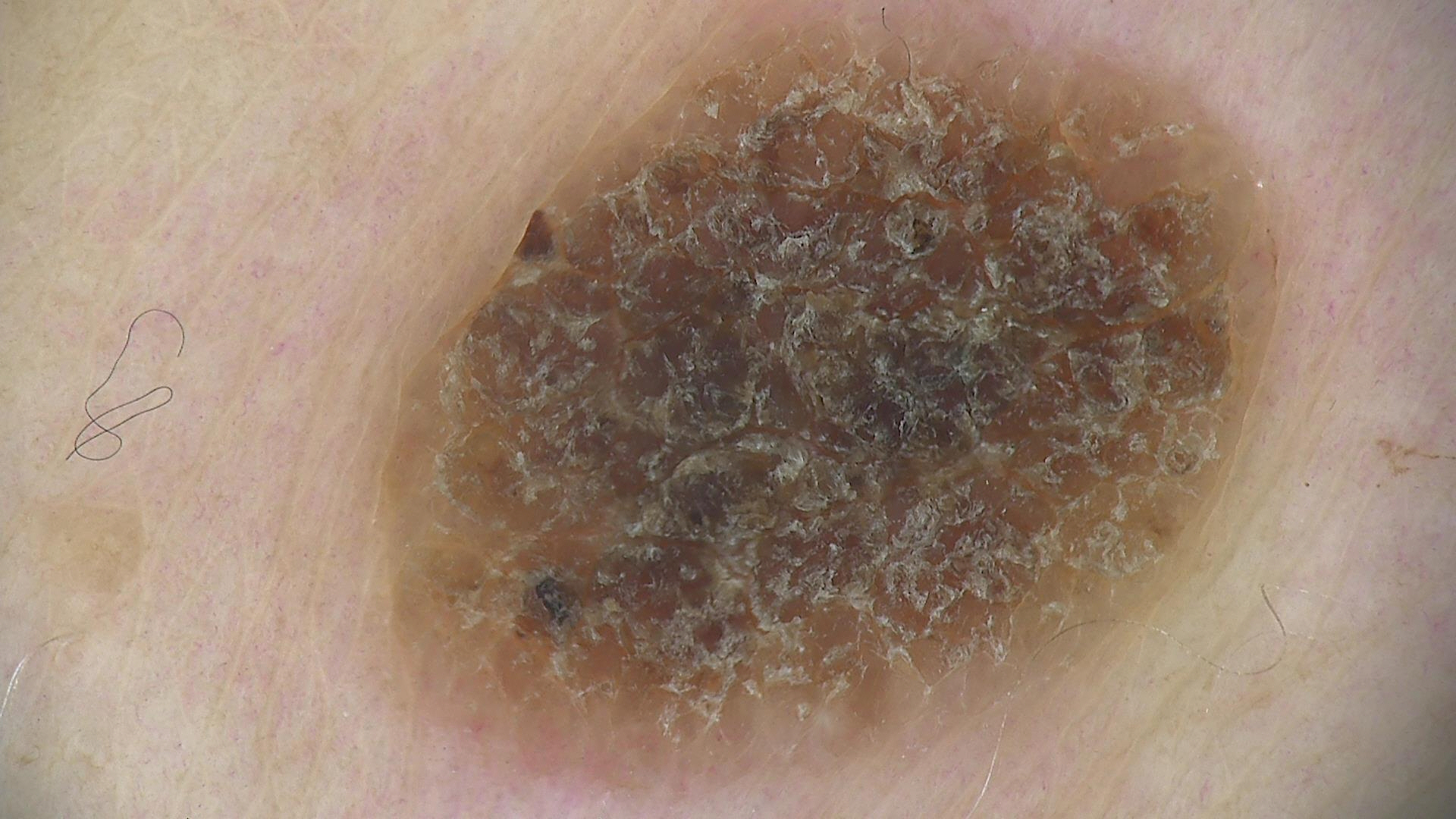image type=dermatoscopy; lesion type=keratinocytic; diagnosis=seborrheic keratosis (expert consensus).